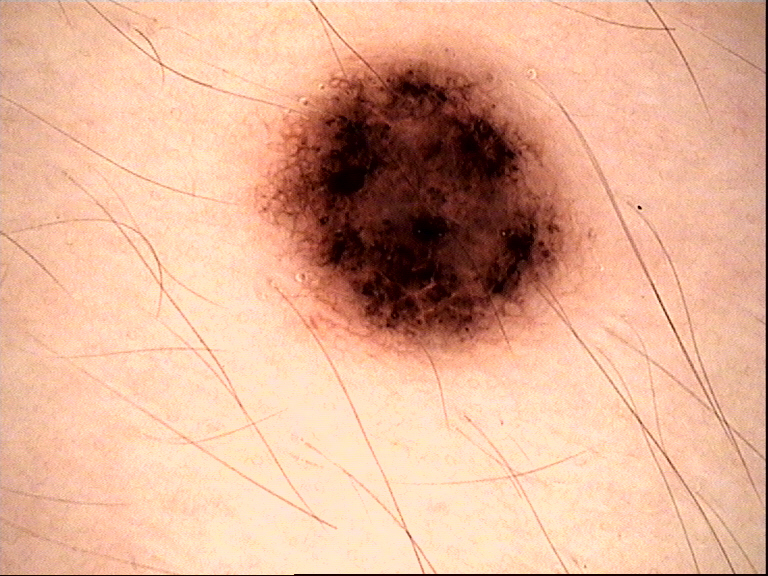Findings:
A dermoscopic close-up of a skin lesion.
Conclusion:
The diagnostic label was a benign lesion — a dysplastic compound nevus.